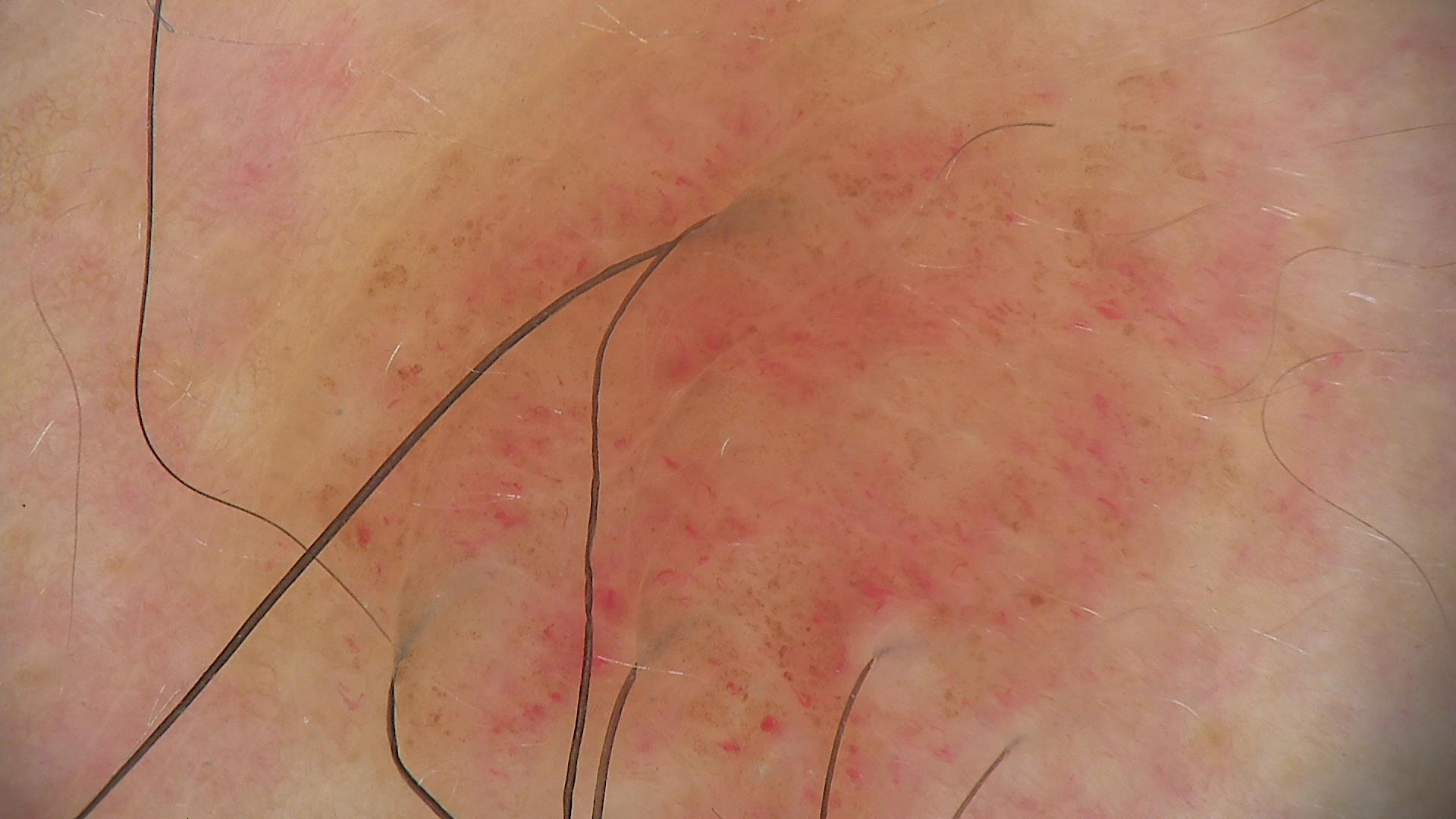Case:
A dermoscopy image of a single skin lesion.
Impression:
Consistent with a banal lesion — a compound nevus.